A dermoscopic close-up of a skin lesion: 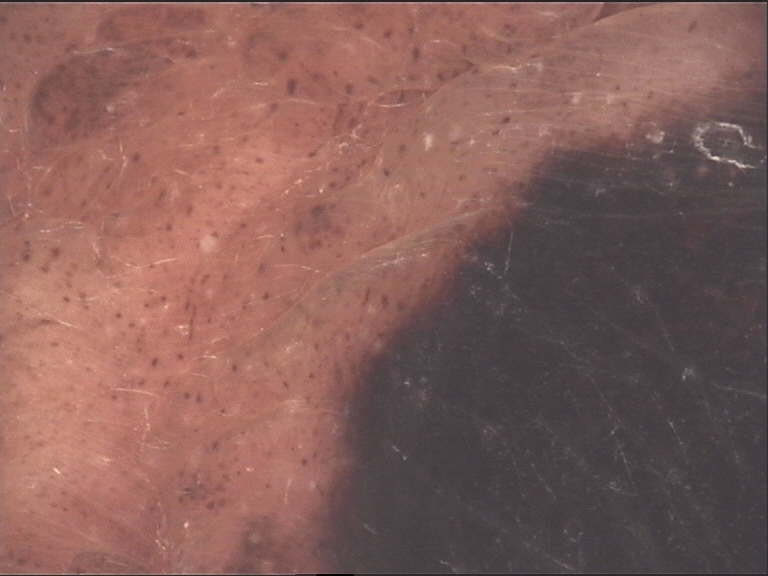This is a banal lesion.
Diagnosed as a congenital compound nevus.